A skin lesion imaged with a dermatoscope:
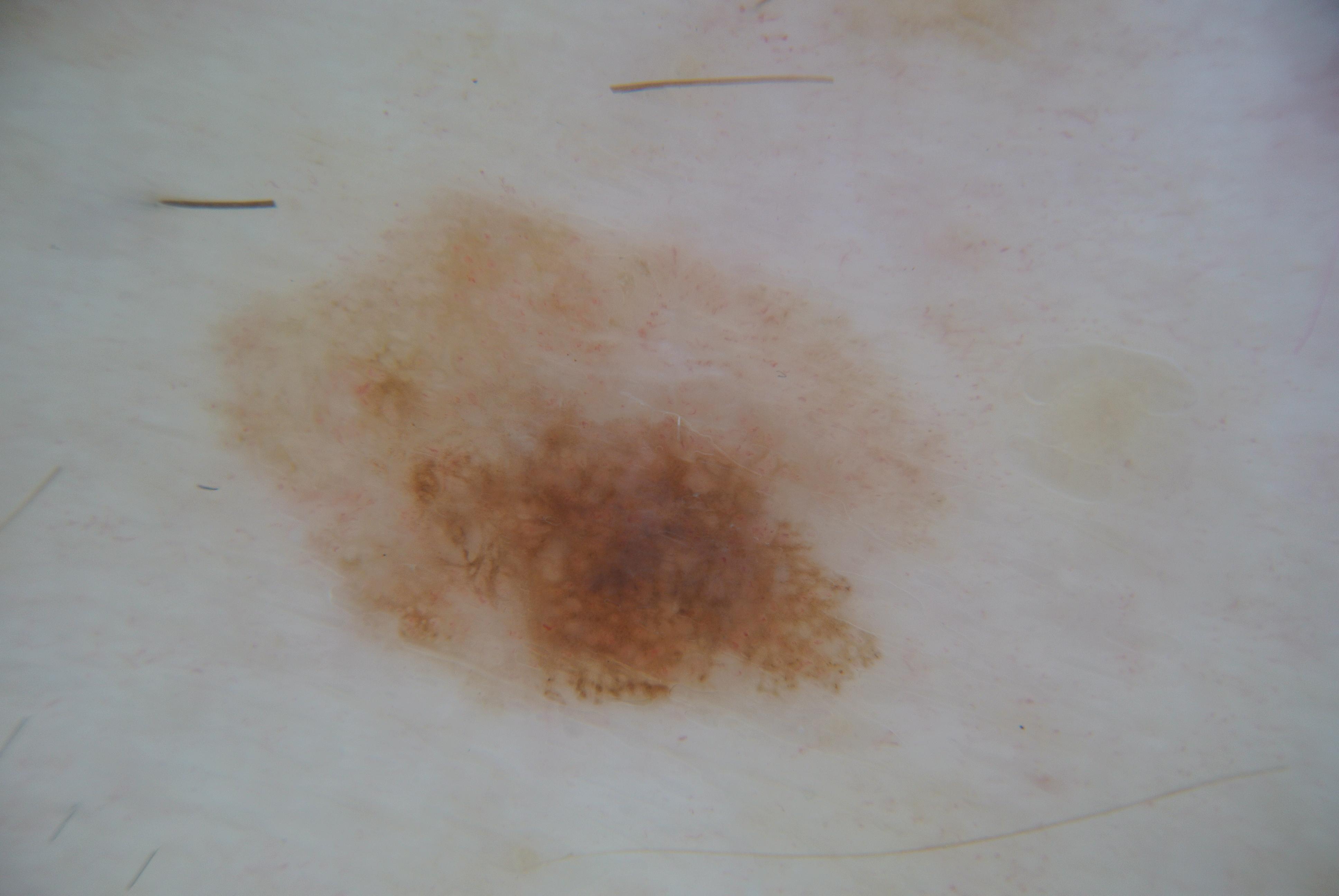Notes:
• lesion location: bbox(198, 167, 961, 720)
• diagnostic label: a skin cancer